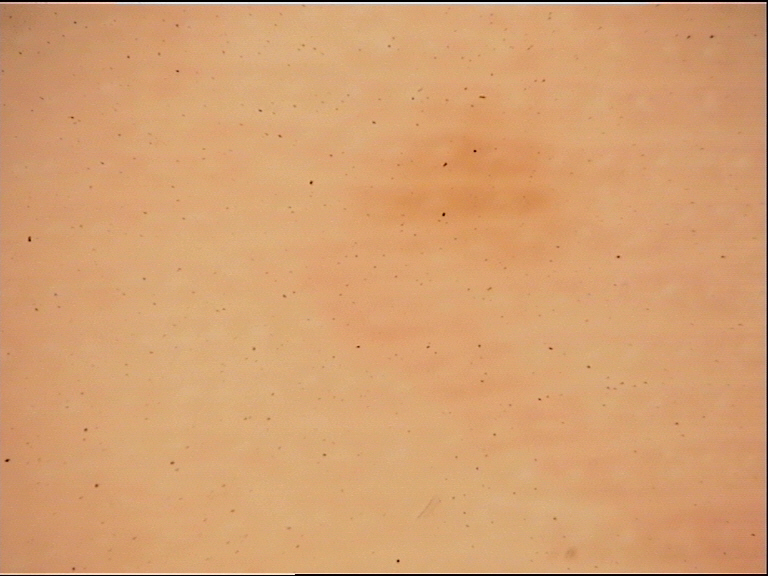<dermoscopy>
  <lesion_type>
    <main_class>banal</main_class>
    <pattern>junctional</pattern>
  </lesion_type>
  <diagnosis>
    <name>acral junctional nevus</name>
    <code>ajb</code>
    <malignancy>benign</malignancy>
    <super_class>melanocytic</super_class>
    <confirmation>expert consensus</confirmation>
  </diagnosis>
</dermoscopy>